This image was taken at an angle. Human graders estimated MST 3 (US pool) or 2 (India pool):
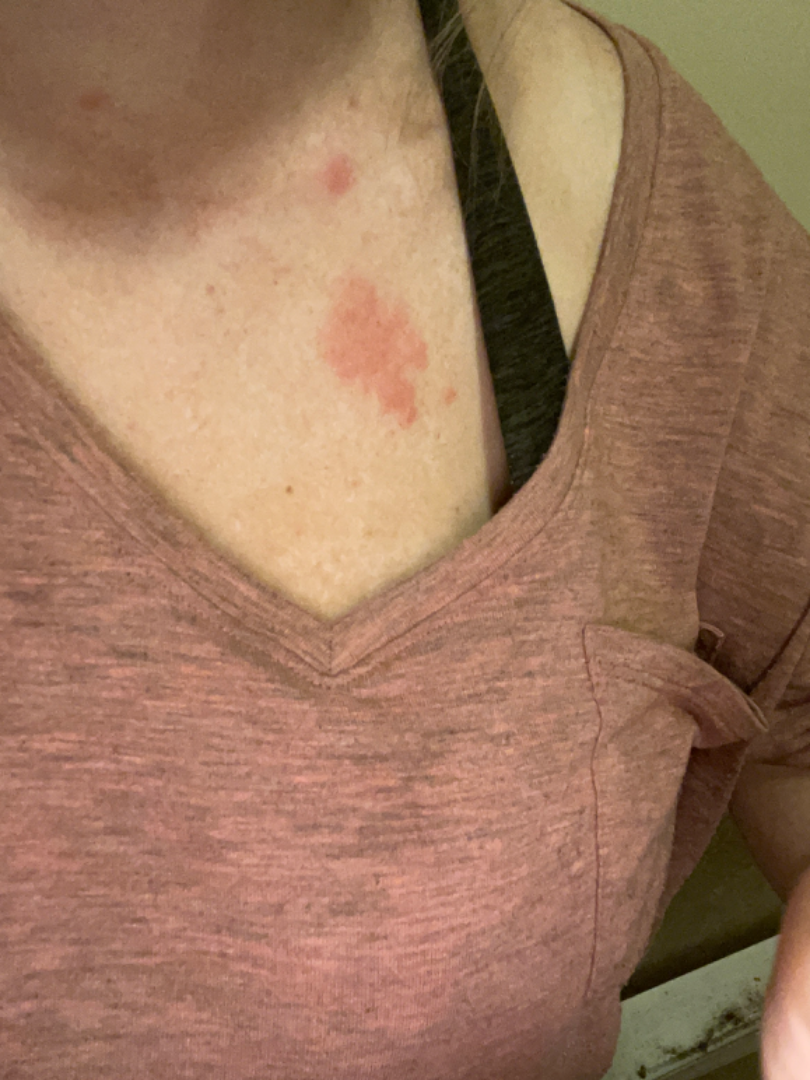The leading consideration is Insect Bite; an alternative is Urticaria; less probable is Allergic Contact Dermatitis.